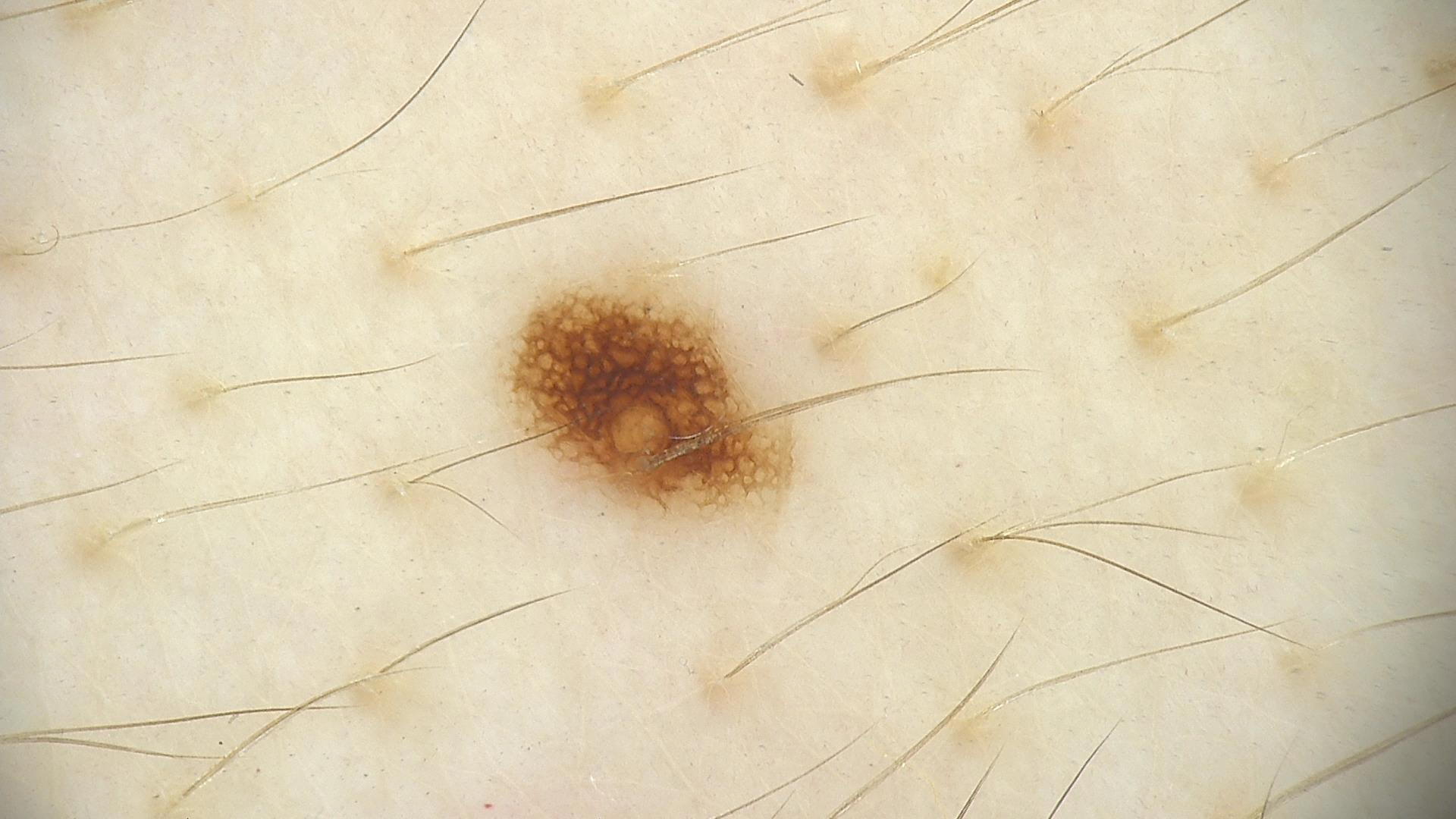Case:
A skin lesion imaged with a dermatoscope.
Conclusion:
Labeled as a benign lesion — a dysplastic junctional nevus.